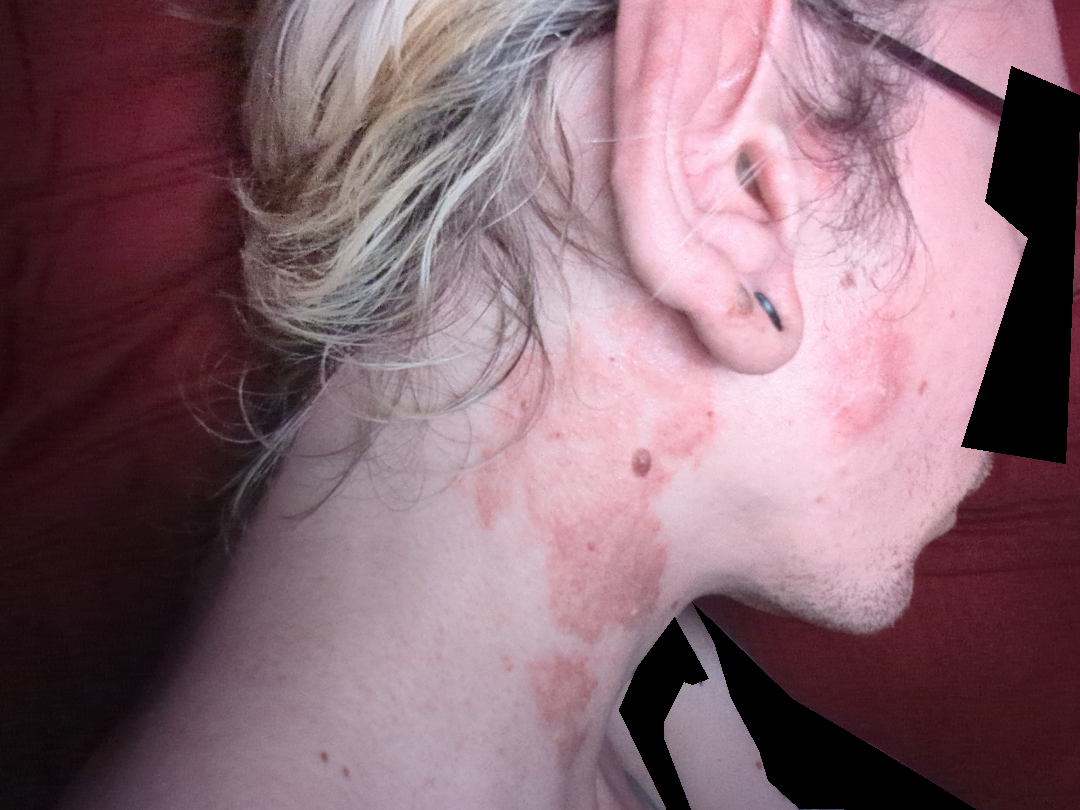Skin tone: FST I; lay graders estimated Monk skin tone scale 2. Reported duration is since childhood. The lesion is described as flat and raised or bumpy. An image taken at a distance. Symptoms reported: darkening. Located on the head or neck. The patient considered this a pigmentary problem. The subject is a male aged 18–29. The reviewing clinician's impression was: Tinea, Allergic Contact Dermatitis and Cutaneous lupus were each considered, in no particular order.